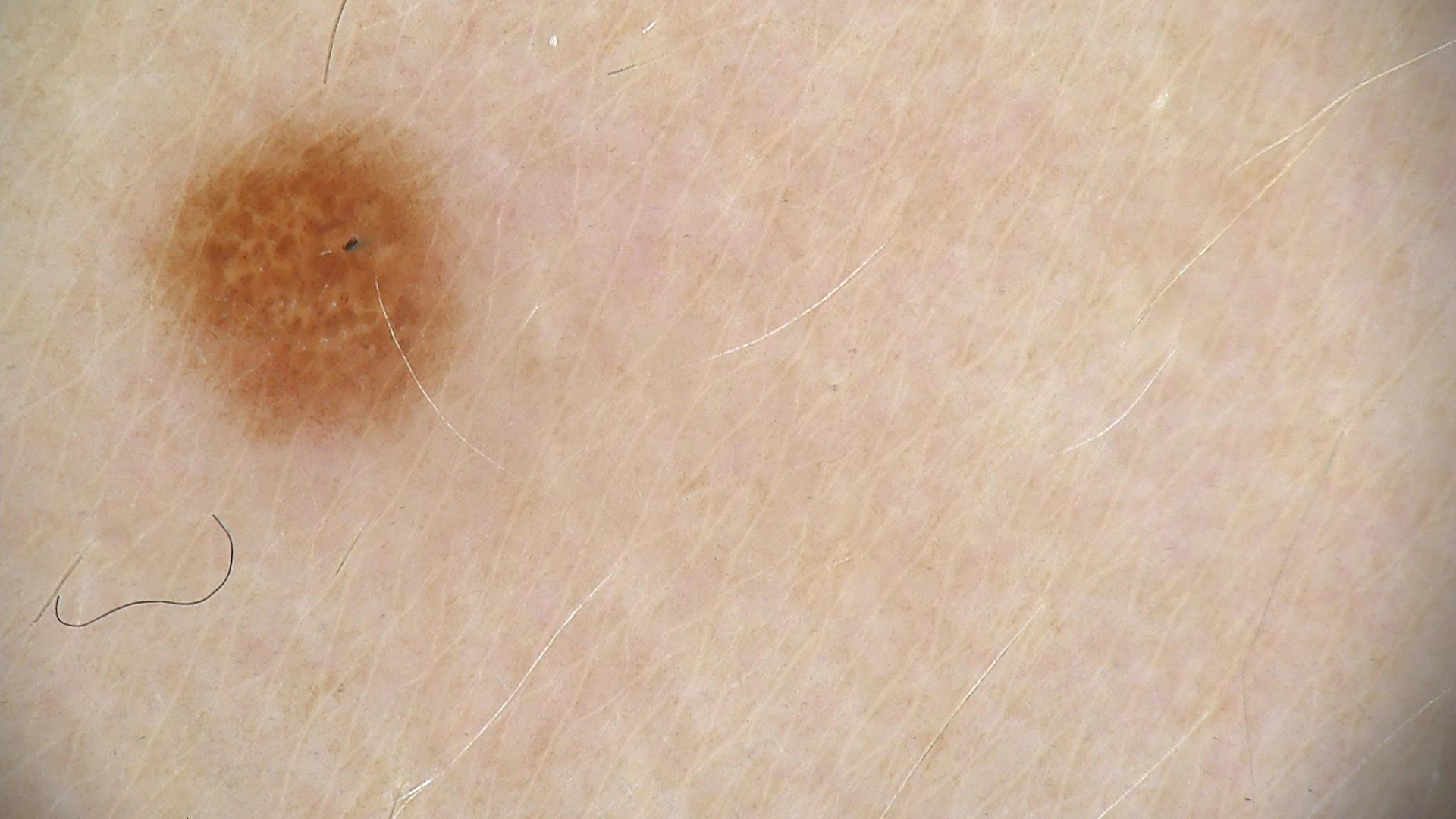A dermoscopic photograph of a skin lesion. Diagnosed as a dysplastic junctional nevus.